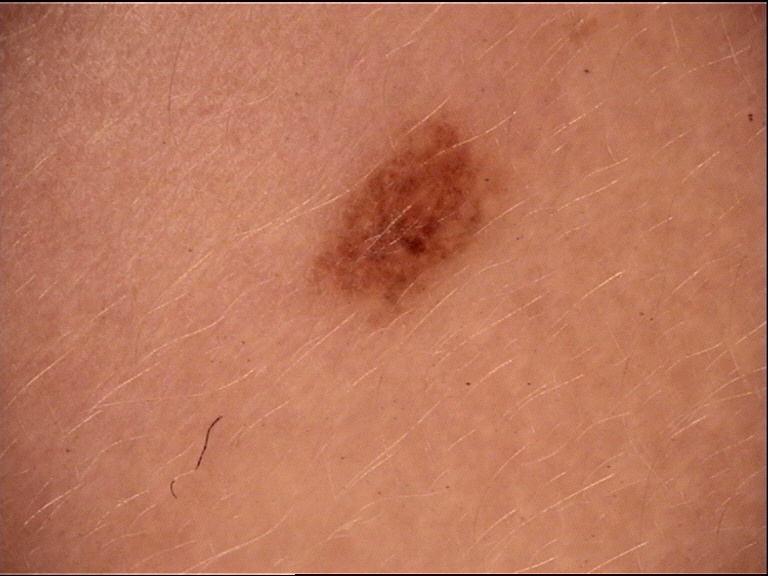Case:
– diagnostic label · dysplastic junctional nevus (expert consensus)